A dermoscopic close-up of a skin lesion.
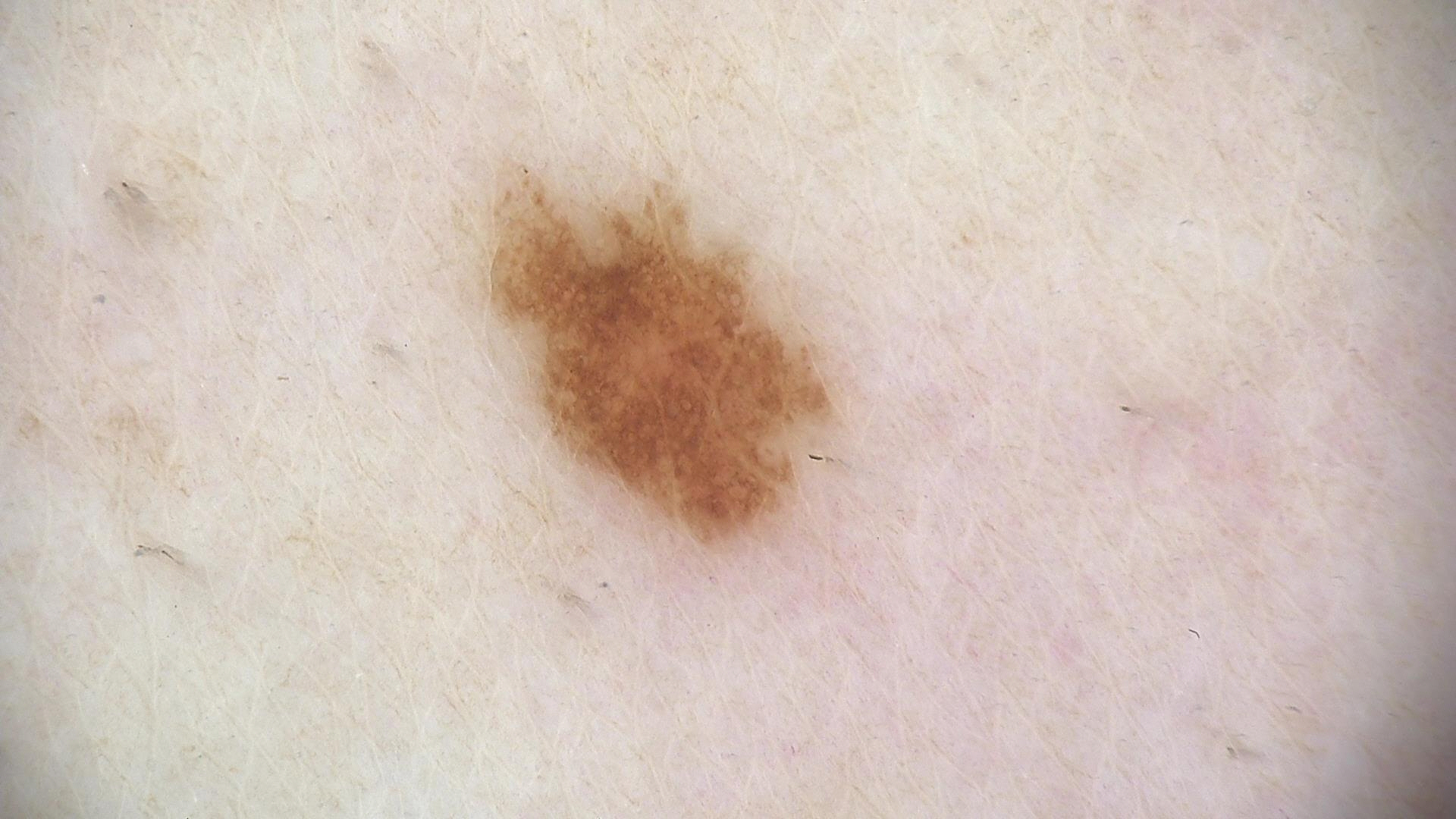Impression:
The diagnostic label was a dysplastic junctional nevus.